Located on the arm; close-up view:
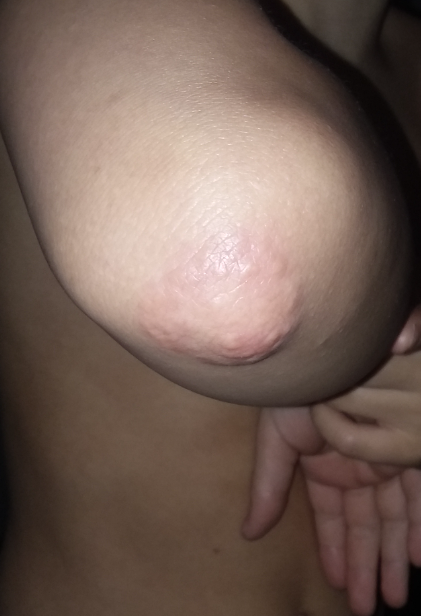<report>
<texture>raised or bumpy</texture>
<skin_tone>
  <fitzpatrick>III</fitzpatrick>
</skin_tone>
<patient_category>a rash</patient_category>
<differential>
  <leading>Granuloma annulare</leading>
  <considered>Urticaria, Hypersensitivity</considered>
</differential>
</report>